A dermoscopic close-up of a skin lesion:
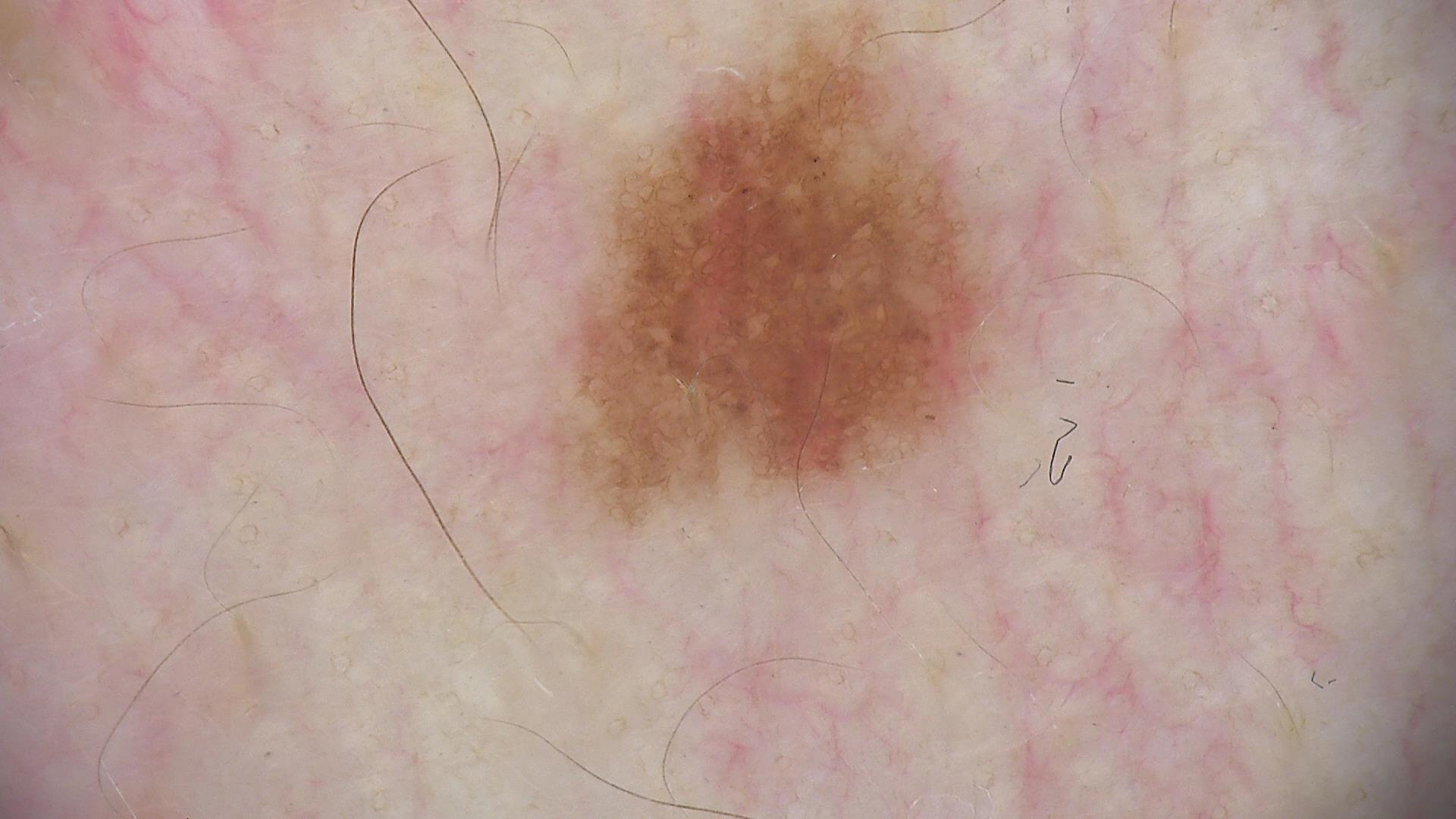Impression: The diagnosis was a dysplastic junctional nevus.